The chart notes prior skin cancer (patient or family), pesticide exposure, and prior malignancy (patient or family): 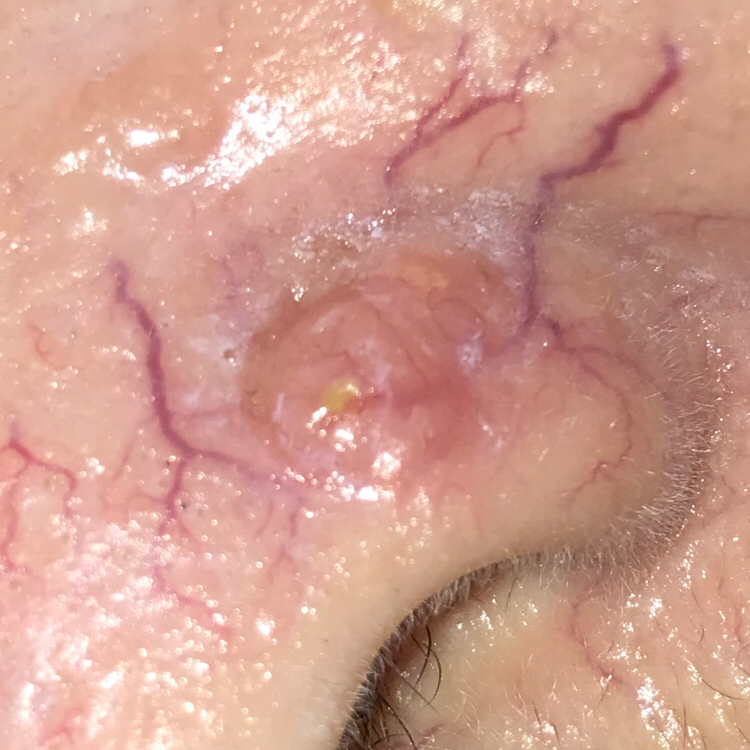Notes:
* site — the nose
* size — approx. 10 × 6 mm
* diagnosis — basal cell carcinoma (biopsy-proven)